By history, prior malignancy (patient or family) and pesticide exposure. A clinical close-up photograph of a skin lesion. Skin type II. A female patient 53 years of age:
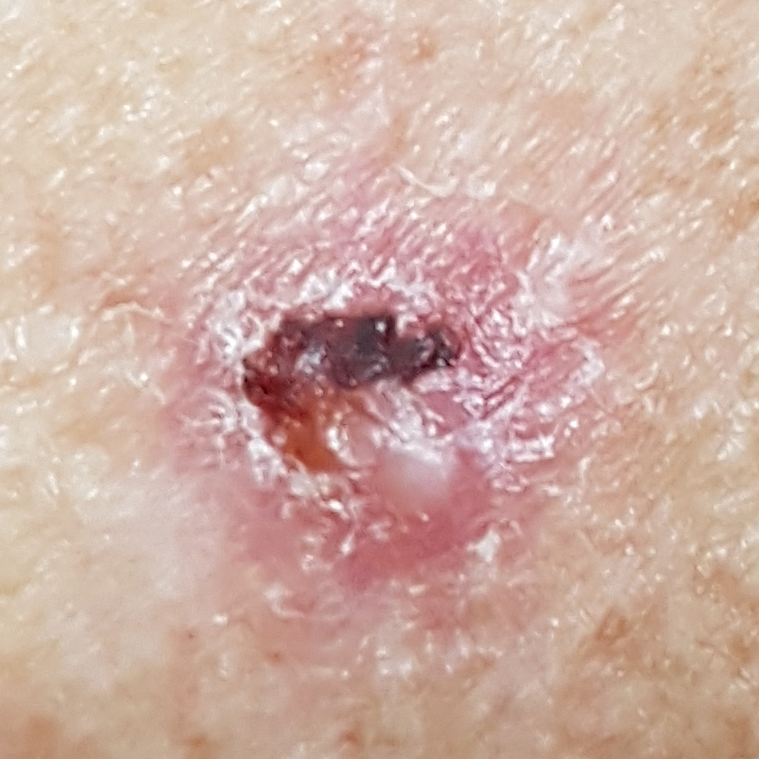Q: What is the anatomic site?
A: the back
Q: Lesion size?
A: 10 × 9 mm
Q: What does the patient describe?
A: itching, bleeding, elevation, growth, pain / no change in appearance
Q: What is this lesion?
A: basal cell carcinoma (biopsy-proven)